Close-up view, the affected area is the palm — 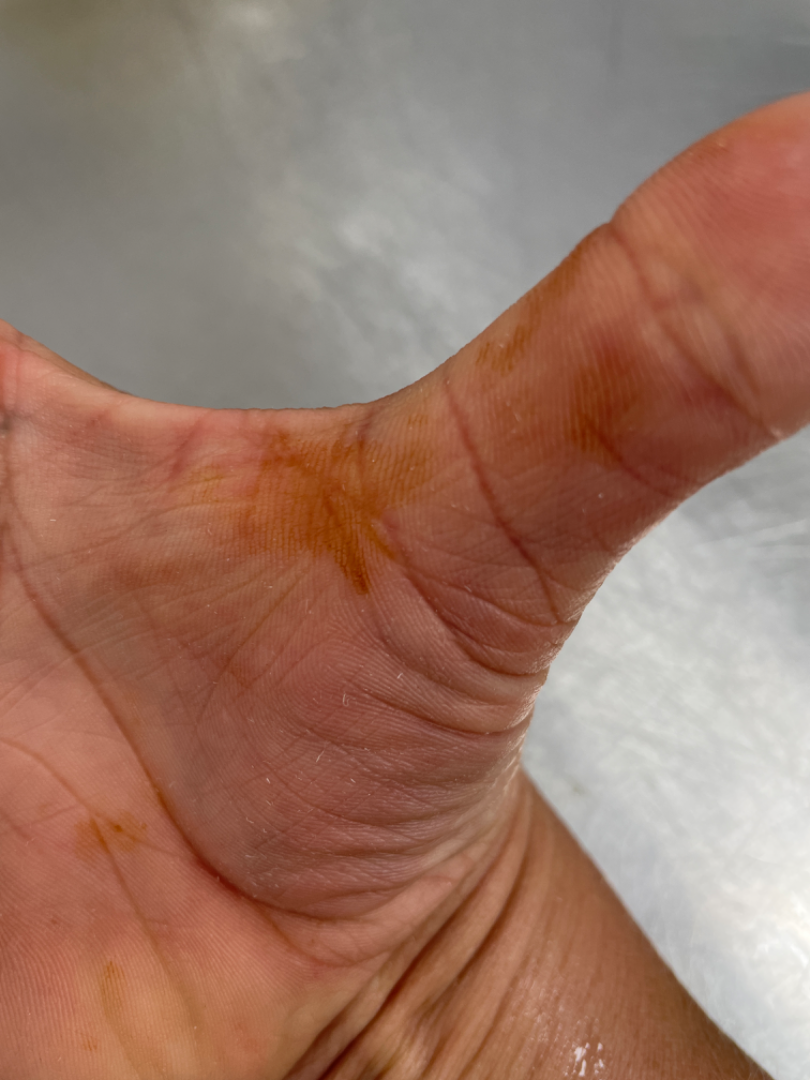Review: Diagnostic features were not clearly distinguishable in this photograph. Patient information: The patient reported no relevant symptoms from the lesion. The lesion is described as flat.